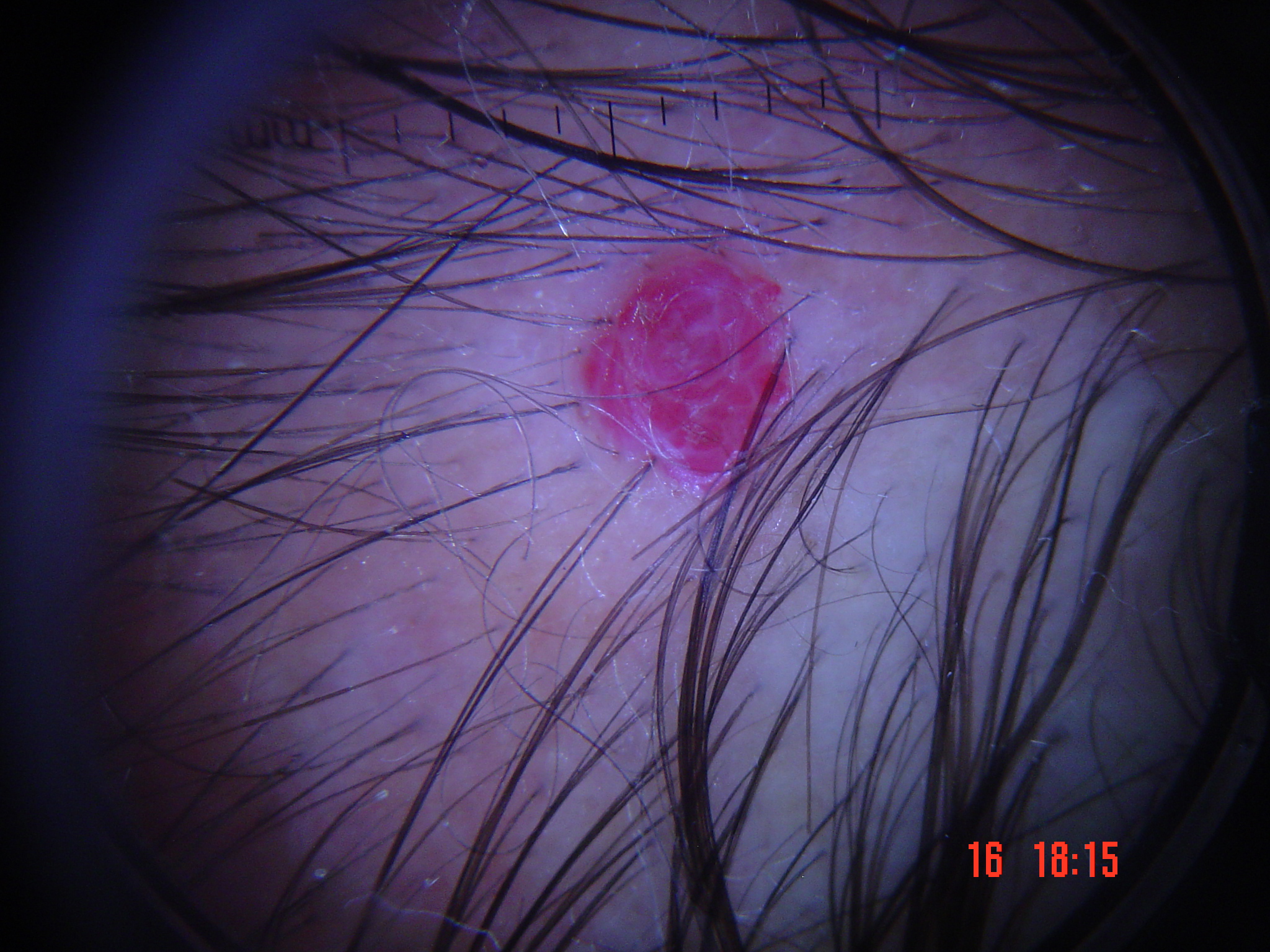modality: dermoscopy
category: vascular
diagnostic label: hemangioma (expert consensus)